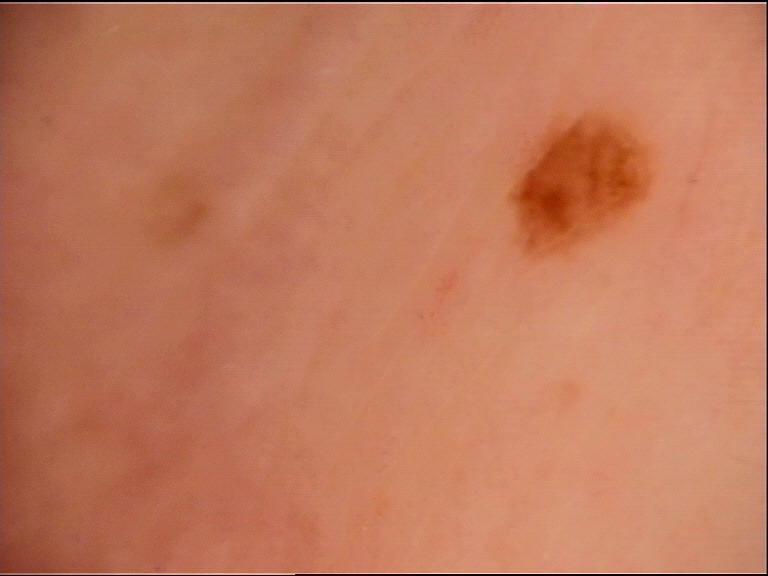{
  "diagnosis": {
    "name": "junctional nevus",
    "code": "jb",
    "malignancy": "benign",
    "super_class": "melanocytic",
    "confirmation": "expert consensus"
  }
}